A dermoscopic close-up of a skin lesion:
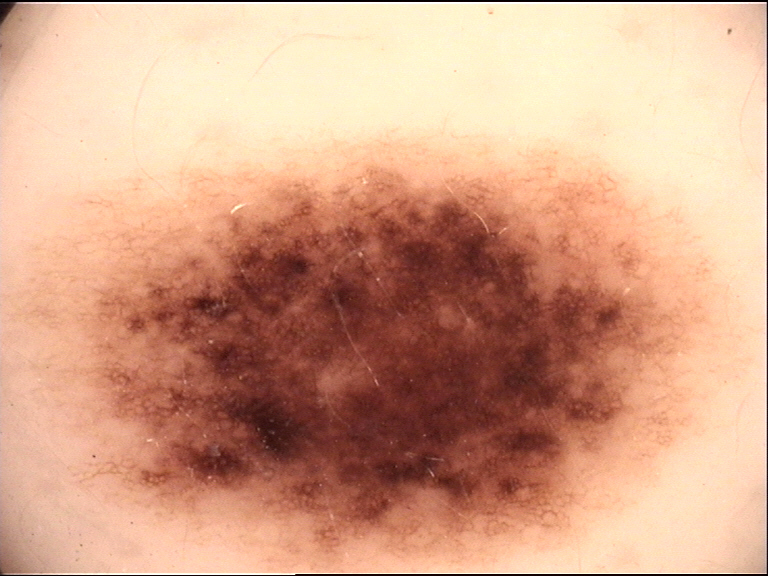{"diagnosis": {"name": "dysplastic junctional nevus", "code": "jd", "malignancy": "benign", "super_class": "melanocytic", "confirmation": "expert consensus"}}